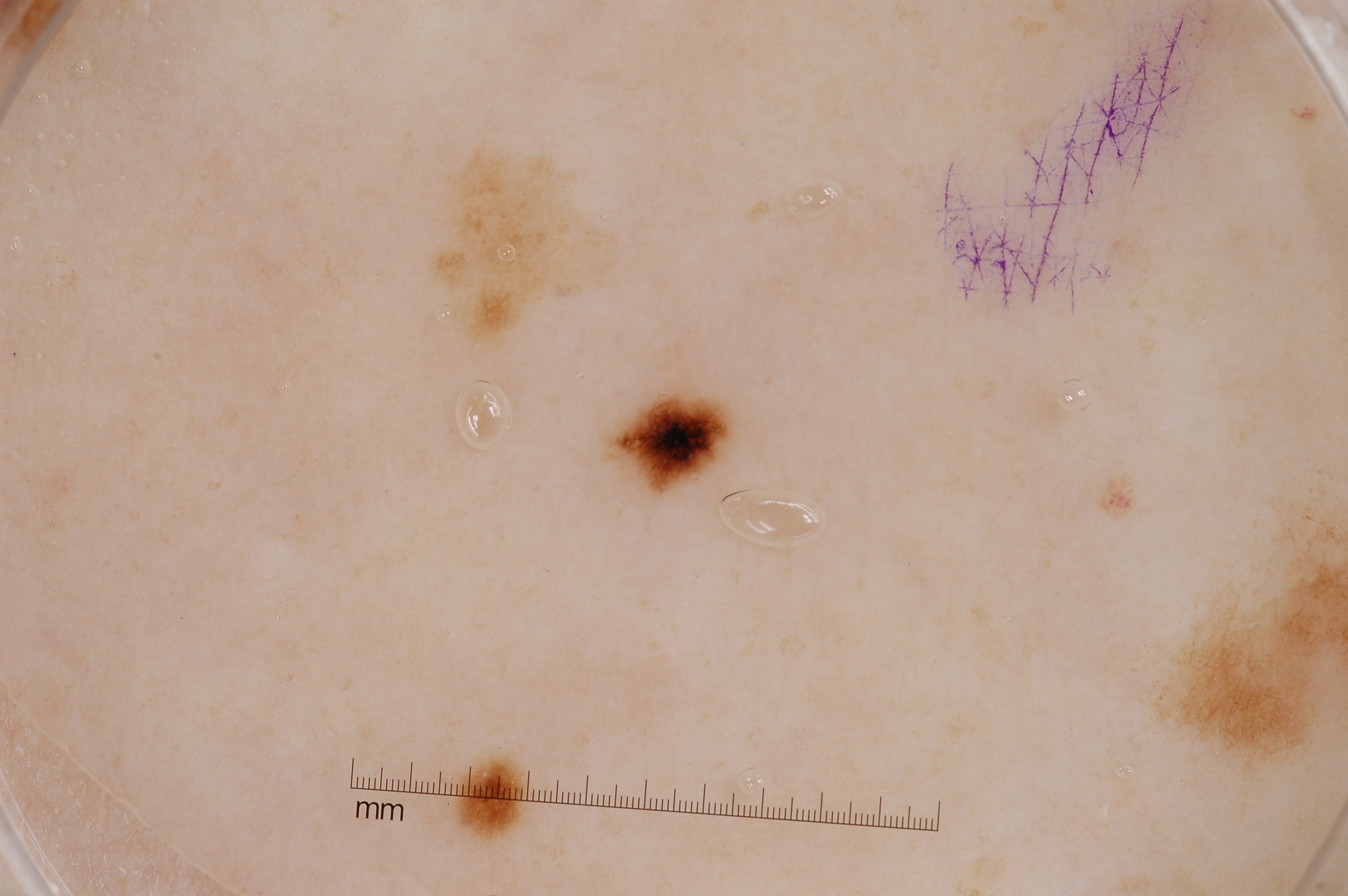{
  "patient": {
    "sex": "female",
    "age_approx": 45
  },
  "image": {
    "modality": "dermoscopy"
  },
  "lesion_location": {
    "bbox_xyxy": [
      595,
      388,
      737,
      509
    ]
  },
  "lesion_extent": {
    "approx_field_fraction_pct": 1
  },
  "dermoscopic_features": {
    "present": [
      "pigment network"
    ],
    "absent": [
      "milia-like cysts",
      "streaks",
      "negative network"
    ]
  },
  "diagnosis": {
    "name": "melanocytic nevus",
    "malignancy": "benign",
    "lineage": "melanocytic",
    "provenance": "clinical"
  }
}